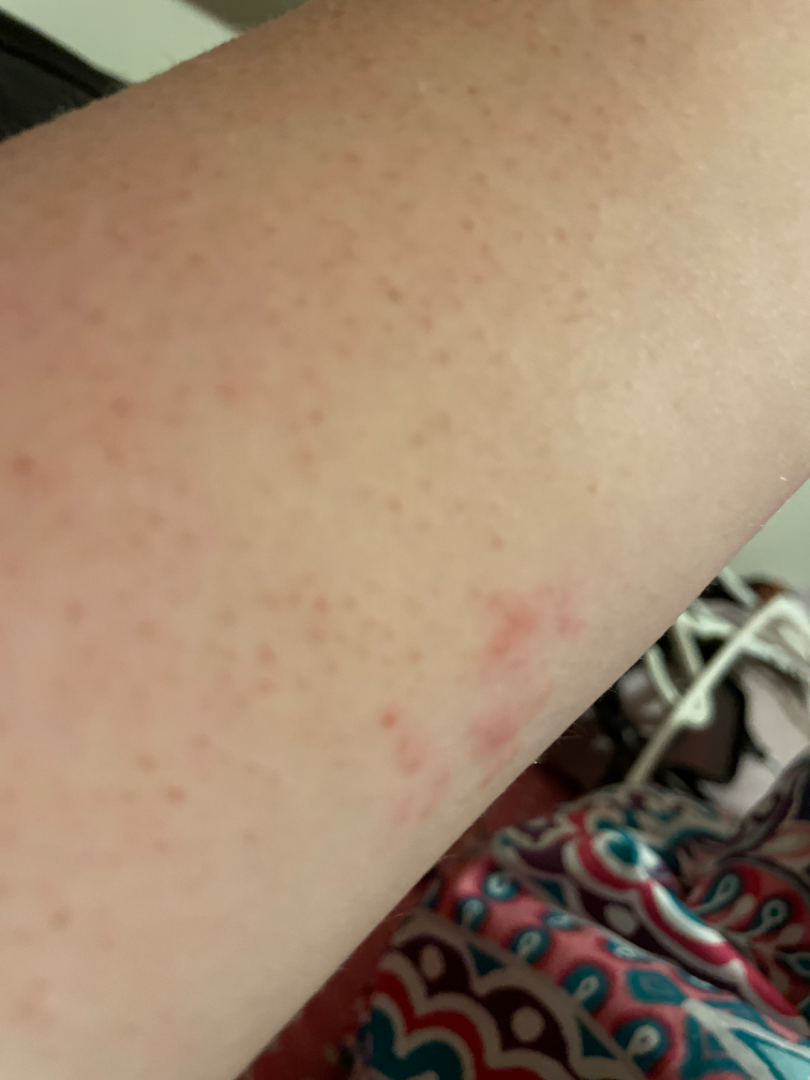Findings:
The skin condition could not be confidently assessed from this image.